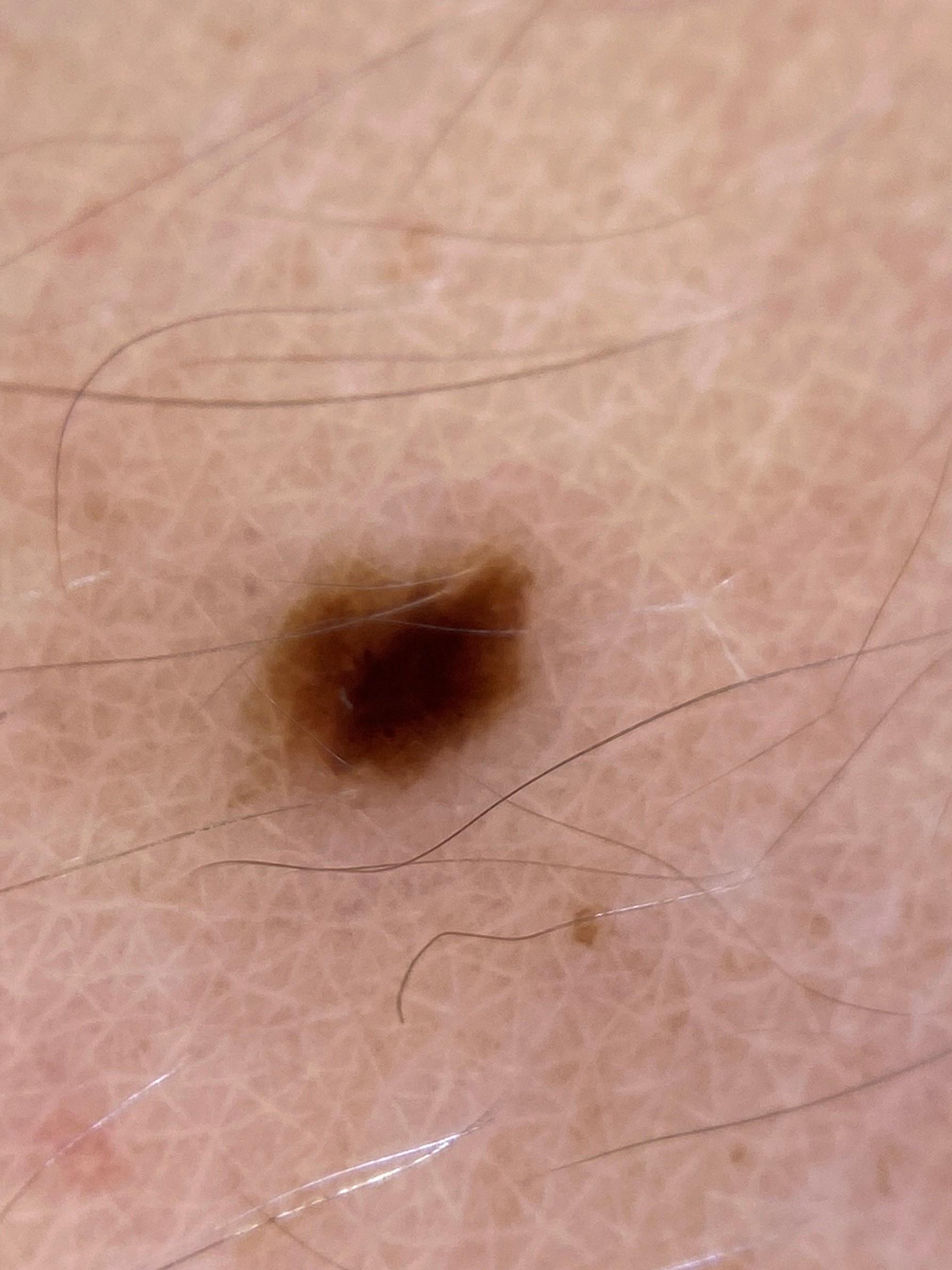Biopsy-confirmed as a nevus.